A male patient 66 years of age; a dermatoscopic image of a skin lesion; the patient describes having few moles overall; by self-report, a prior organ transplant; imaged for a research study, with no referral diagnosis recorded; the patient says their skin reddens with sun exposure.
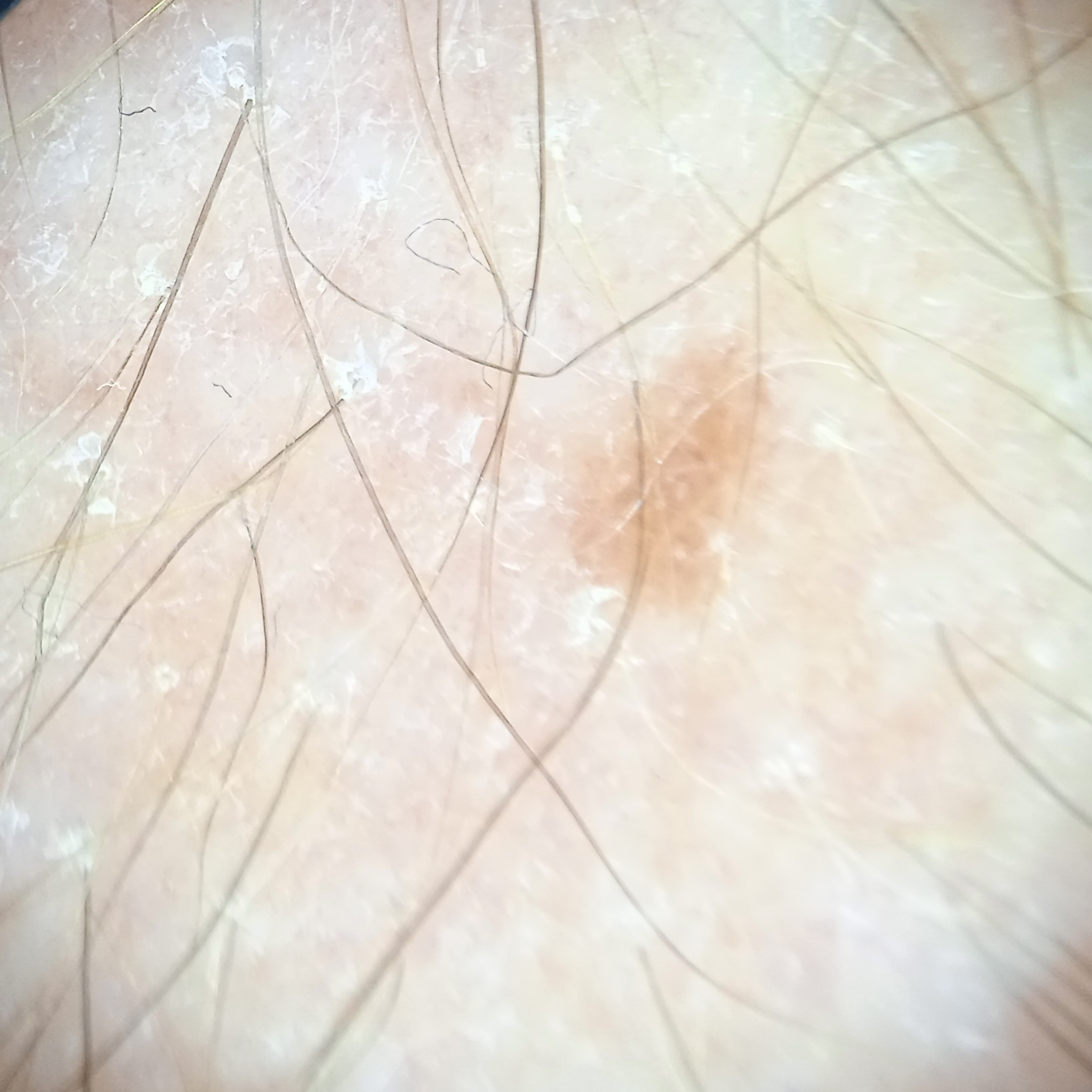– site · an arm
– diameter · 3.4 mm
– assessment · melanocytic nevus (dermatologist consensus)